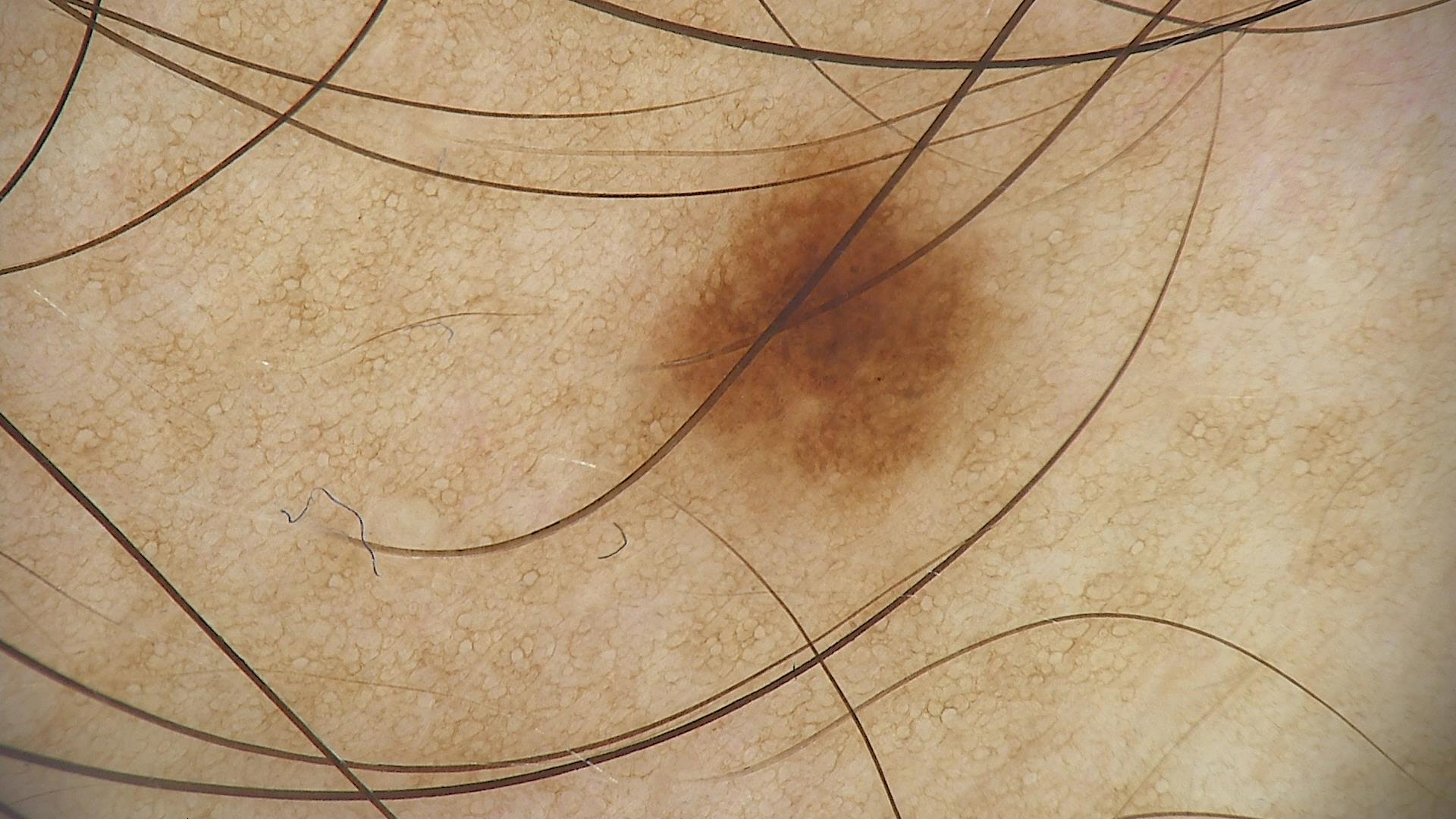label: dysplastic junctional nevus (expert consensus).